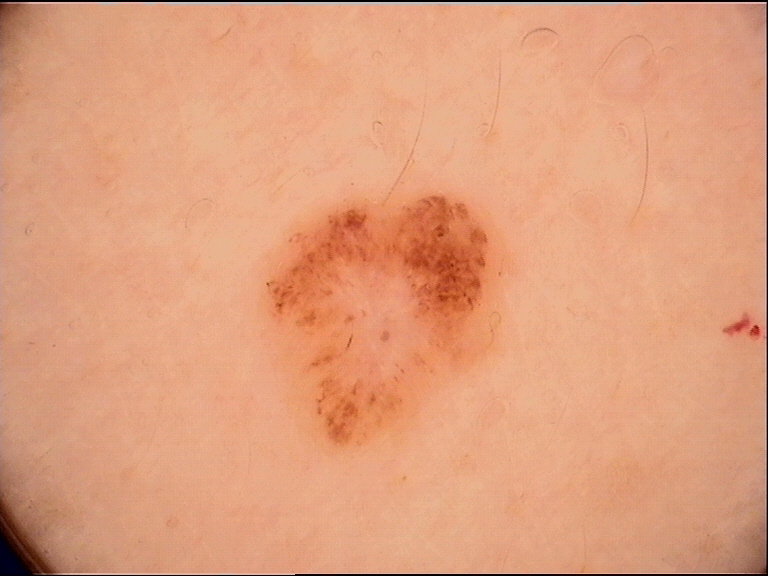A dermoscopic photograph of a skin lesion. Diagnosed as a dysplastic compound nevus.